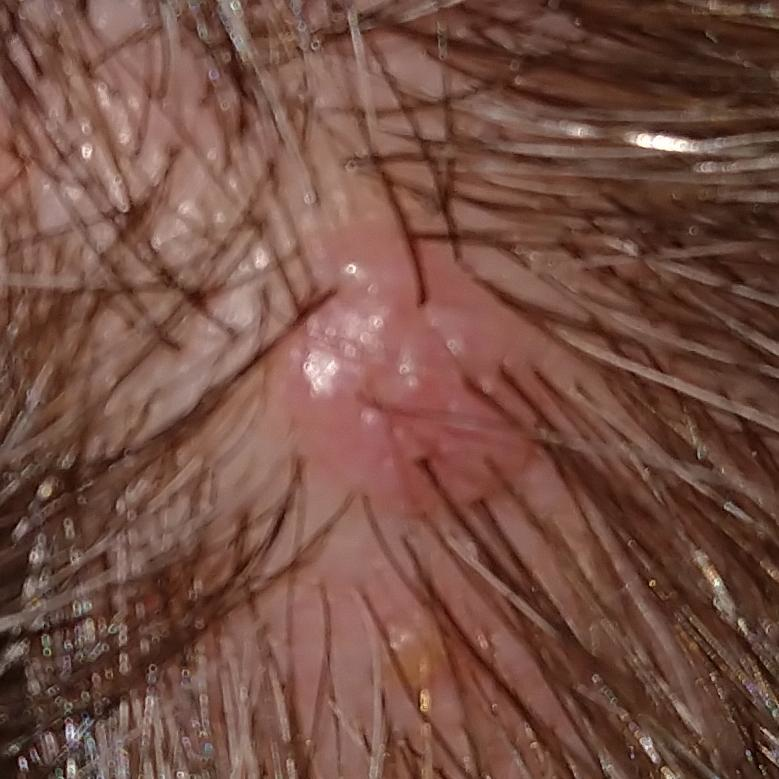Q: Who is the patient?
A: in their 50s
Q: What kind of image is this?
A: clinical photo
Q: Where on the body is the lesion?
A: the scalp
Q: What symptoms does the patient report?
A: elevation, pain, growth / no change in appearance
Q: What is this lesion?
A: nevus (clinical consensus)